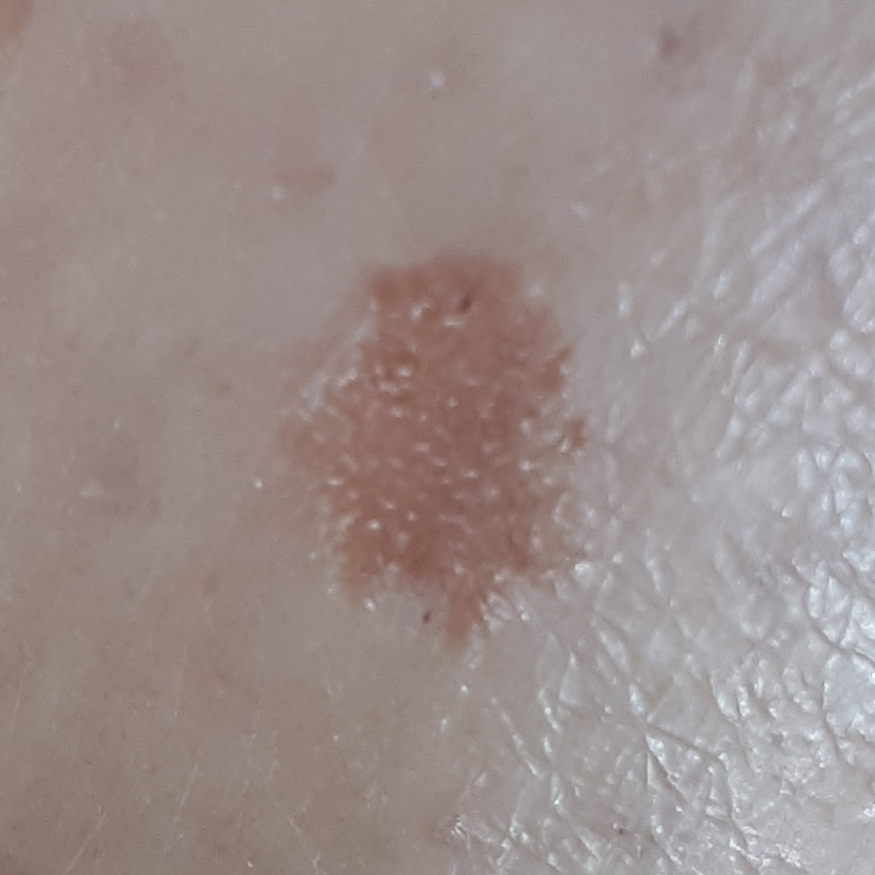A patient in their 30s. Expert review favored a seborrheic keratosis.